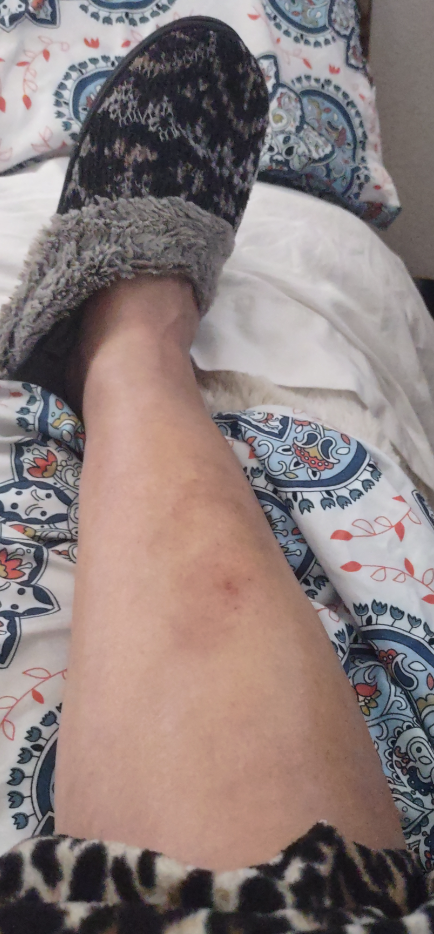{"duration": "more than one year", "body_site": "leg", "shot_type": "at a distance", "systemic_symptoms": ["fatigue", "chills", "joint pain", "shortness of breath"], "symptoms": ["bothersome appearance", "itching", "pain", "darkening", "enlargement", "burning"], "patient": "female", "texture": "rough or flaky", "differential": {"leading": ["Acute and chronic dermatitis"], "considered": ["Morphea/Scleroderma", "Stasis Dermatitis", "Necrobiosis lipoidica"]}}